A dermoscopic image of a skin lesion — 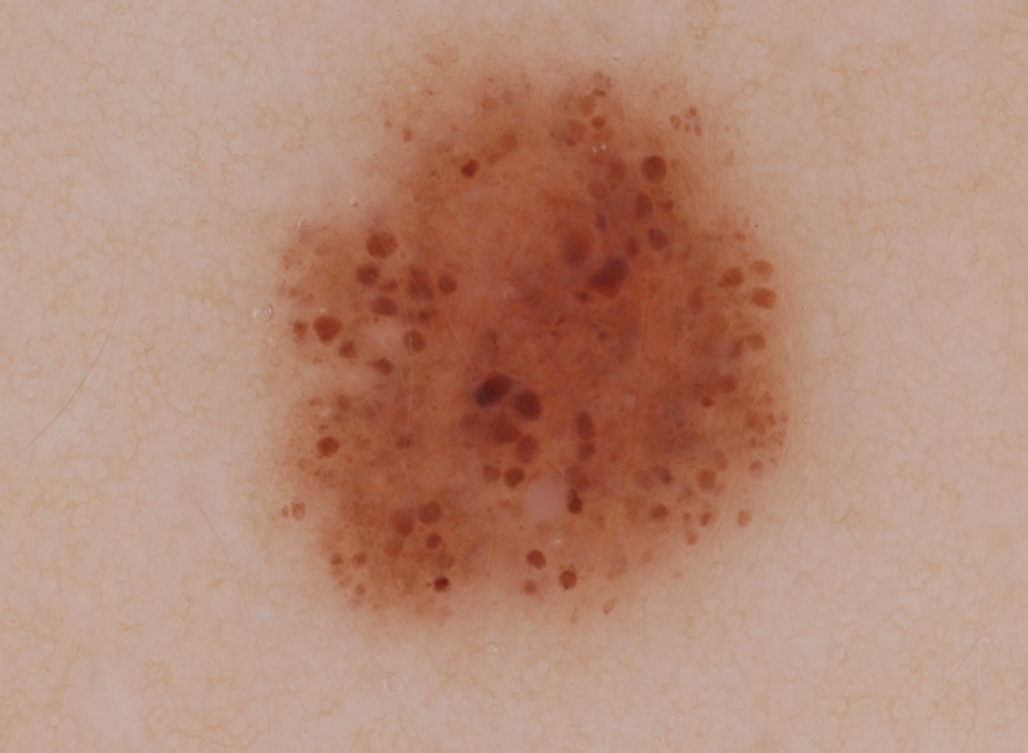lesion location = <box>254, 28, 815, 650</box>
dermoscopic features = milia-like cysts and globules; absent: streaks, negative network, and pigment network
lesion extent = large
diagnostic label = a melanocytic nevus, a benign skin lesion